A dermoscopic image of a skin lesion.
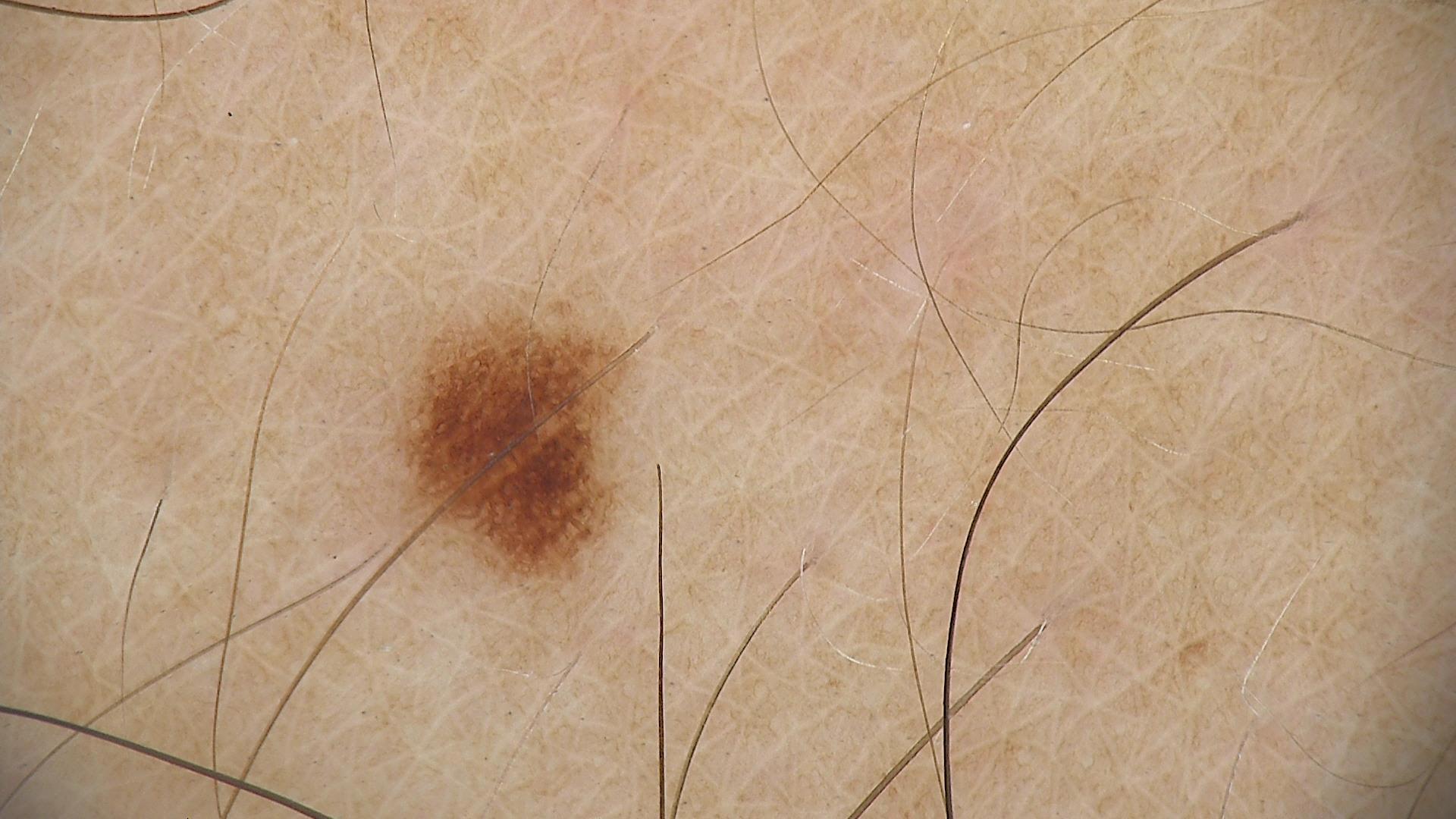diagnostic label: dysplastic junctional nevus (expert consensus).